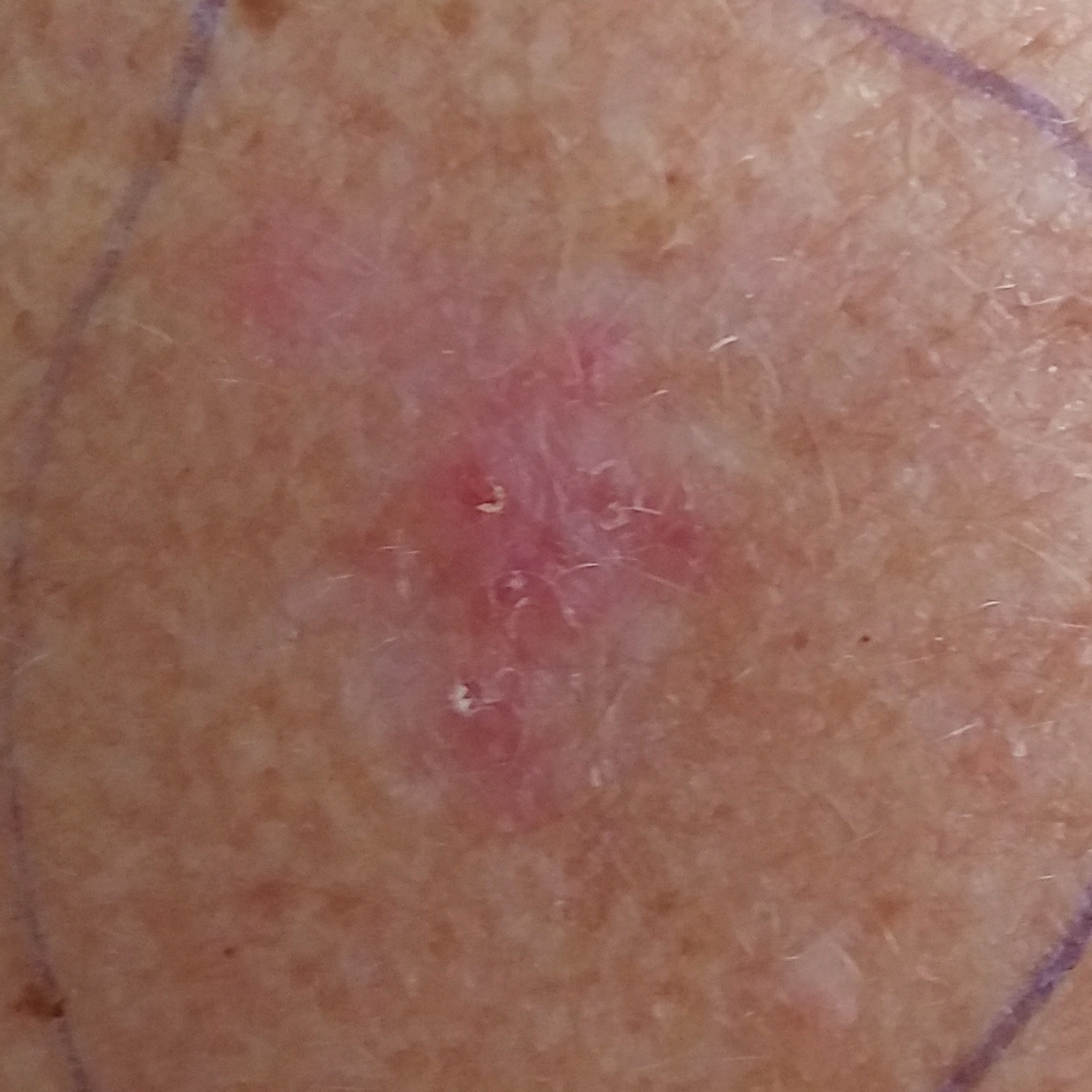The chart notes prior malignancy (patient or family) and prior skin cancer (patient or family). A clinical photograph showing a skin lesion. The patient is Fitzpatrick skin type III. A female patient 55 years old. The lesion is located on the chest. Per patient report, the lesion itches, has grown, and has changed. Biopsy-confirmed as a malignant lesion — a basal cell carcinoma.